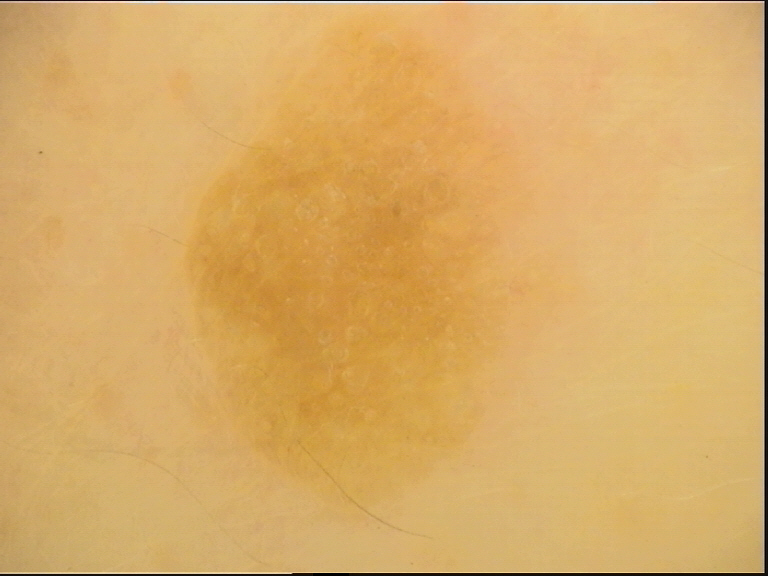image type = dermatoscopy; diagnosis = seborrheic keratosis (expert consensus).